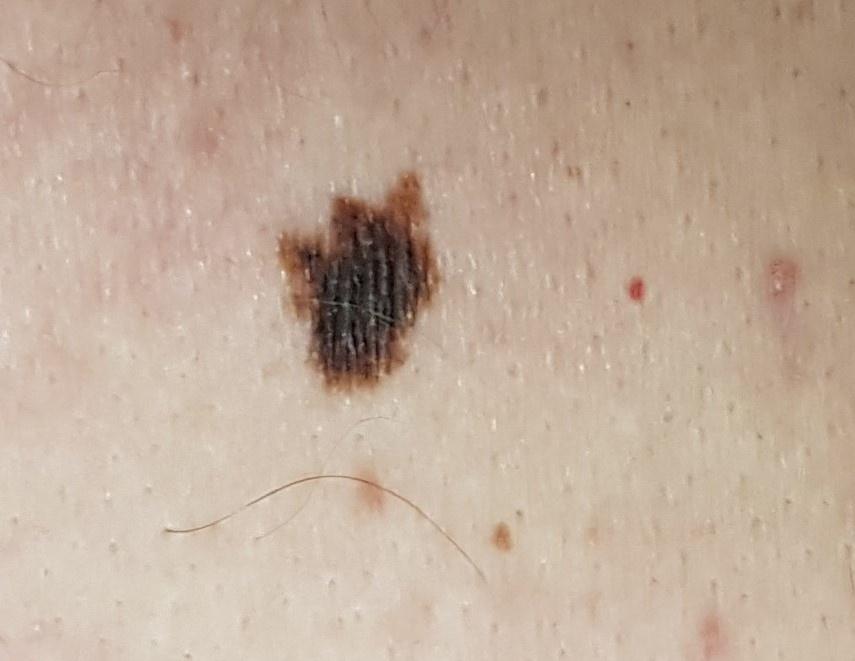Findings:
Per the chart, a prior melanoma. A clinical photograph showing a skin lesion in context. Recorded as Fitzpatrick skin type II.
Diagnosis:
Histopathologically confirmed as a melanoma.